A dermatoscopic image of a skin lesion: 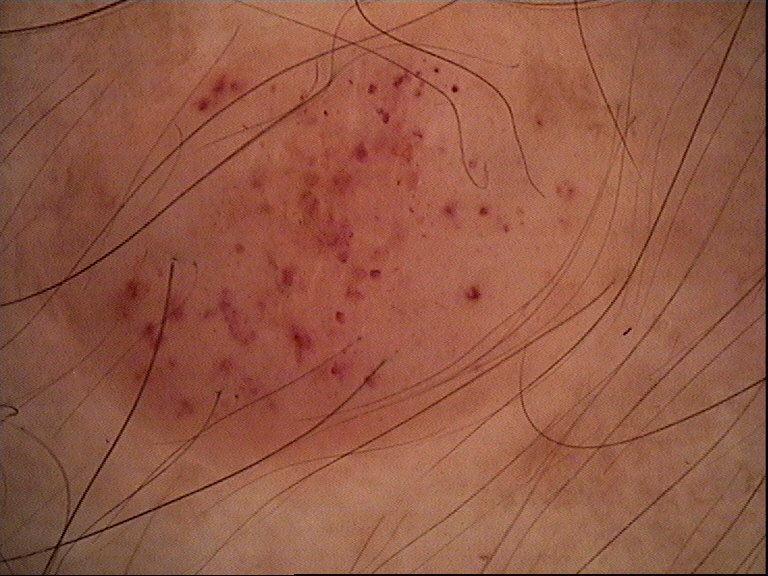Impression: Classified as a hemangioma.